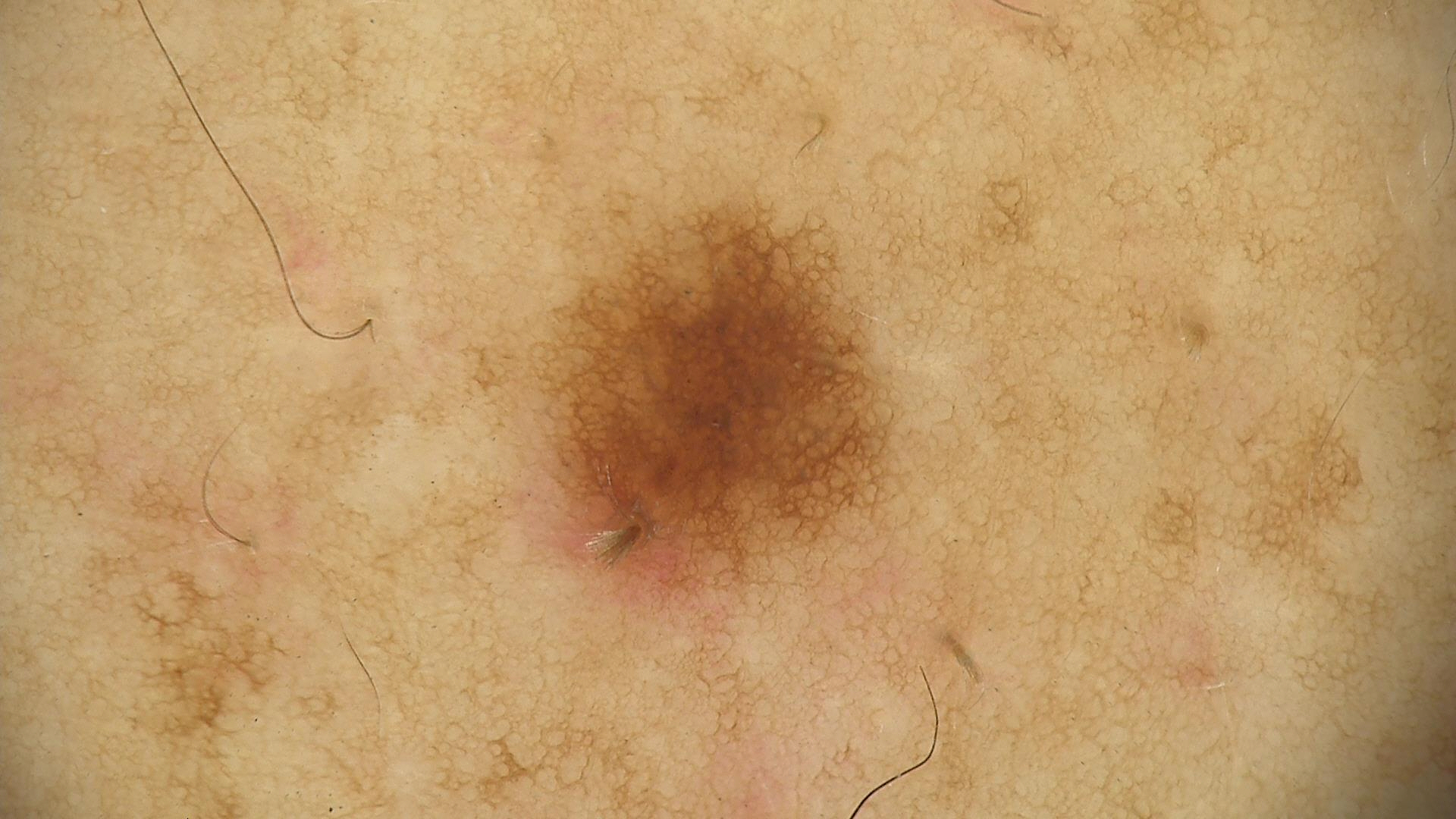Summary: Dermoscopy of a skin lesion. Impression: Diagnosed as a benign lesion — a dysplastic junctional nevus.